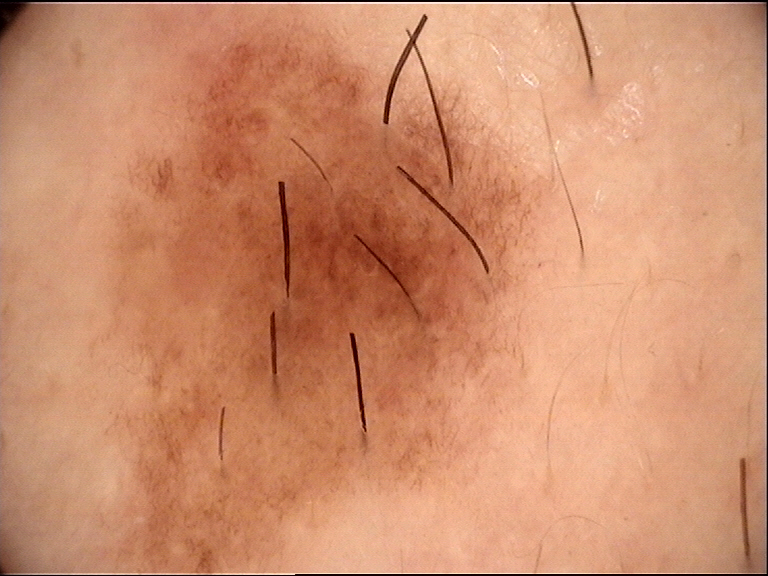Conclusion: Classified as a dysplastic junctional nevus.